A dermatoscopic image of a skin lesion: 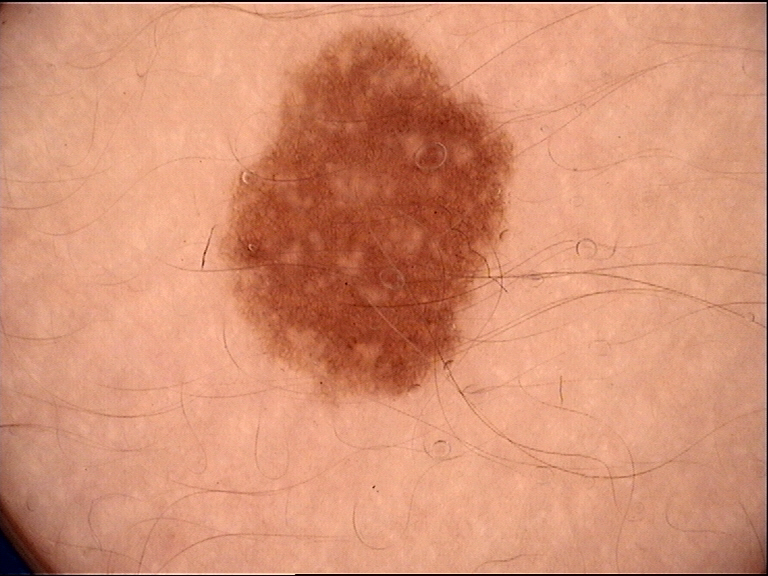<case>
  <lesion_type>
    <main_class>banal</main_class>
    <pattern>junctional</pattern>
  </lesion_type>
  <diagnosis>
    <name>congenital junctional nevus</name>
    <code>cjb</code>
    <malignancy>benign</malignancy>
    <super_class>melanocytic</super_class>
    <confirmation>expert consensus</confirmation>
  </diagnosis>
</case>